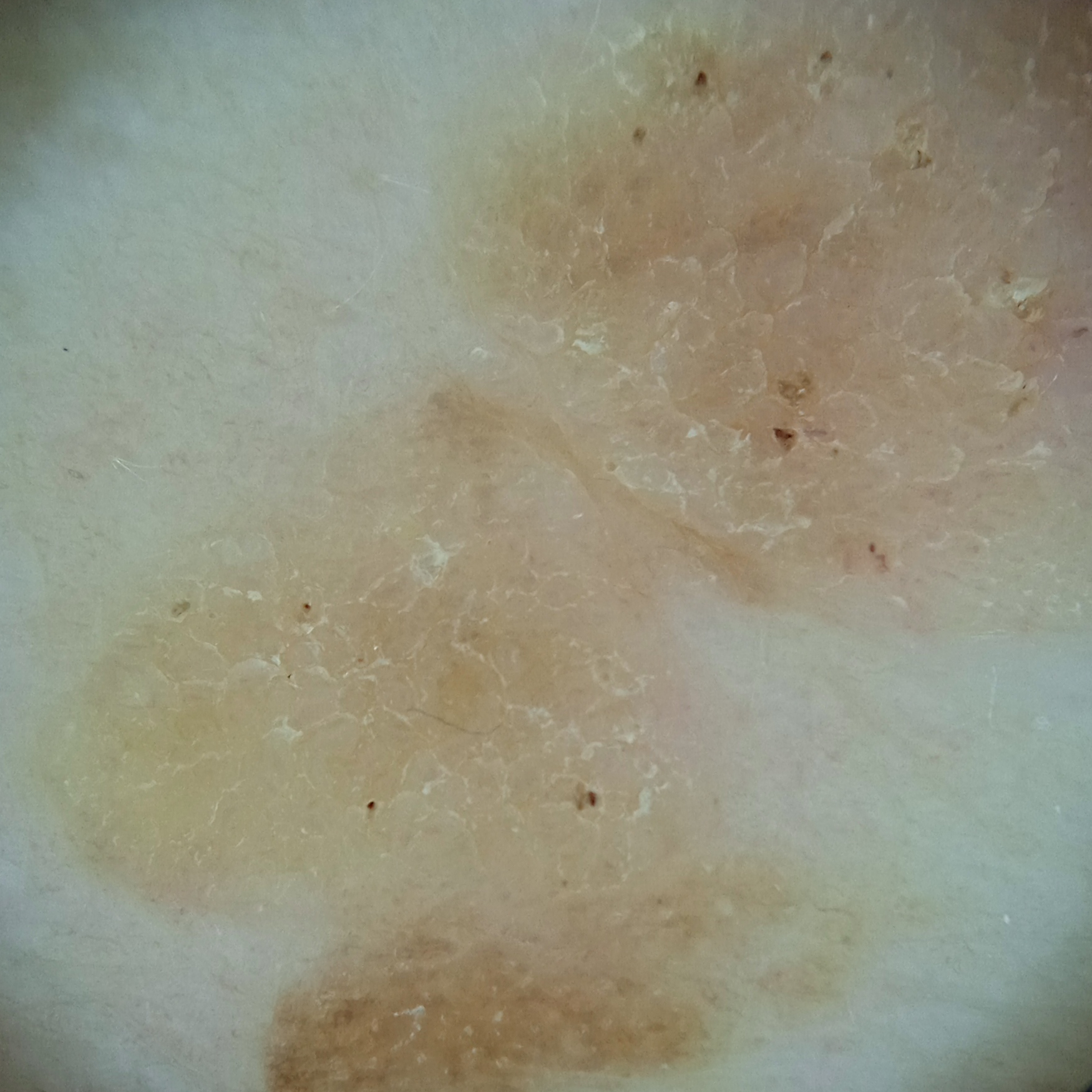{
  "mole_burden": "a moderate number of melanocytic nevi",
  "image": "dermoscopic image",
  "referral": "research study (no referral diagnosis)",
  "patient": {
    "age": 81,
    "sex": "female"
  },
  "lesion_location": "the back",
  "lesion_size": {
    "diameter_mm": 15.5
  },
  "diagnosis": {
    "name": "seborrheic keratosis",
    "malignancy": "benign",
    "unanimous": true,
    "certainty": "good"
  }
}